A patient 52 years of age:
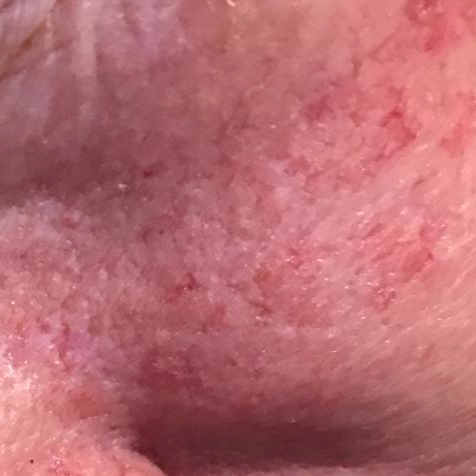Located on the face. The patient reports that the lesion itches. Diagnosed by dermatologist consensus as a lesion of indeterminate malignant potential — an actinic keratosis.